A dermoscopic view of a skin lesion · the patient is a male in their mid- to late 50s.
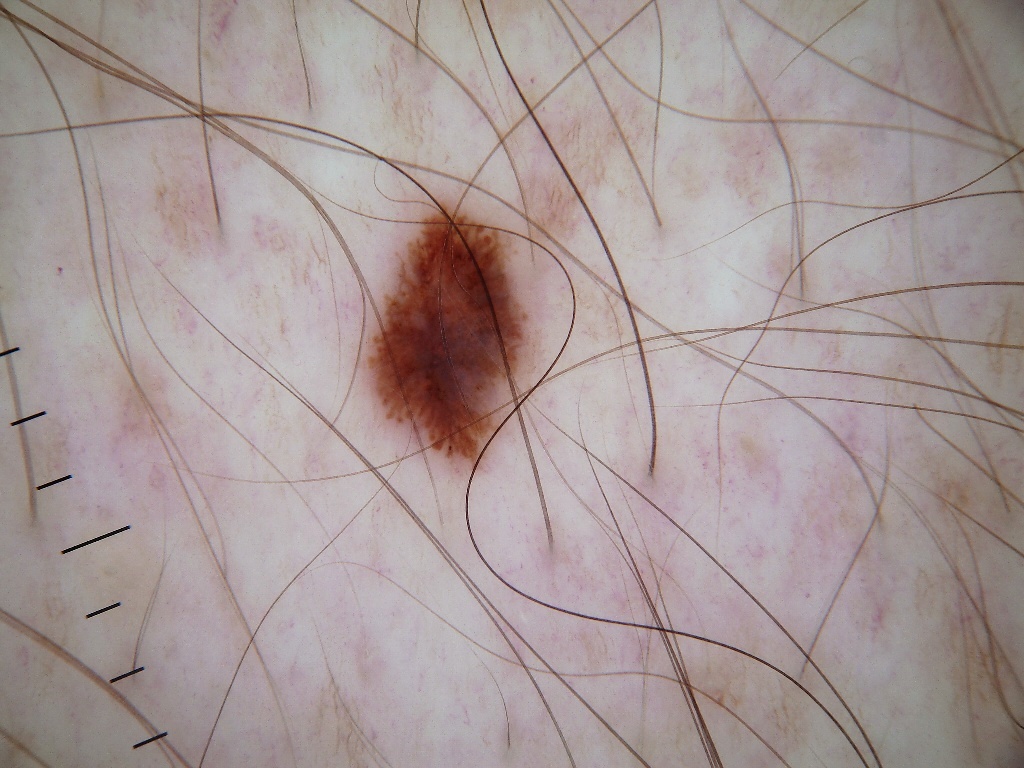Findings: In (x1, y1, x2, y2) order, the lesion spans bbox=[364, 205, 534, 481]. On dermoscopy, the lesion shows globules and streaks. A small lesion occupying a minor part of the field. Pathology: Biopsy-confirmed as a melanoma, a malignant lesion.